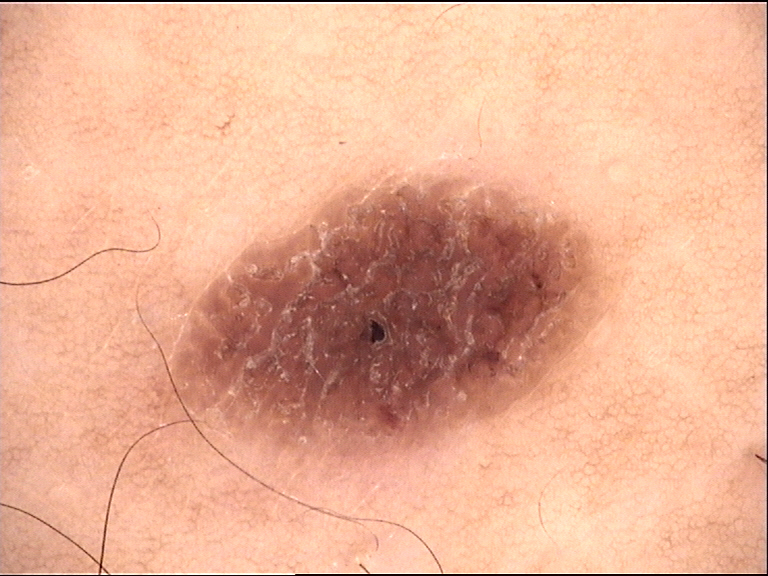Conclusion: Labeled as a benign lesion — a seborrheic keratosis.